Skin tone: Fitzpatrick skin type IV; lay reviewers estimated a Monk Skin Tone of 2, the lesion involves the leg, this image was taken at an angle:
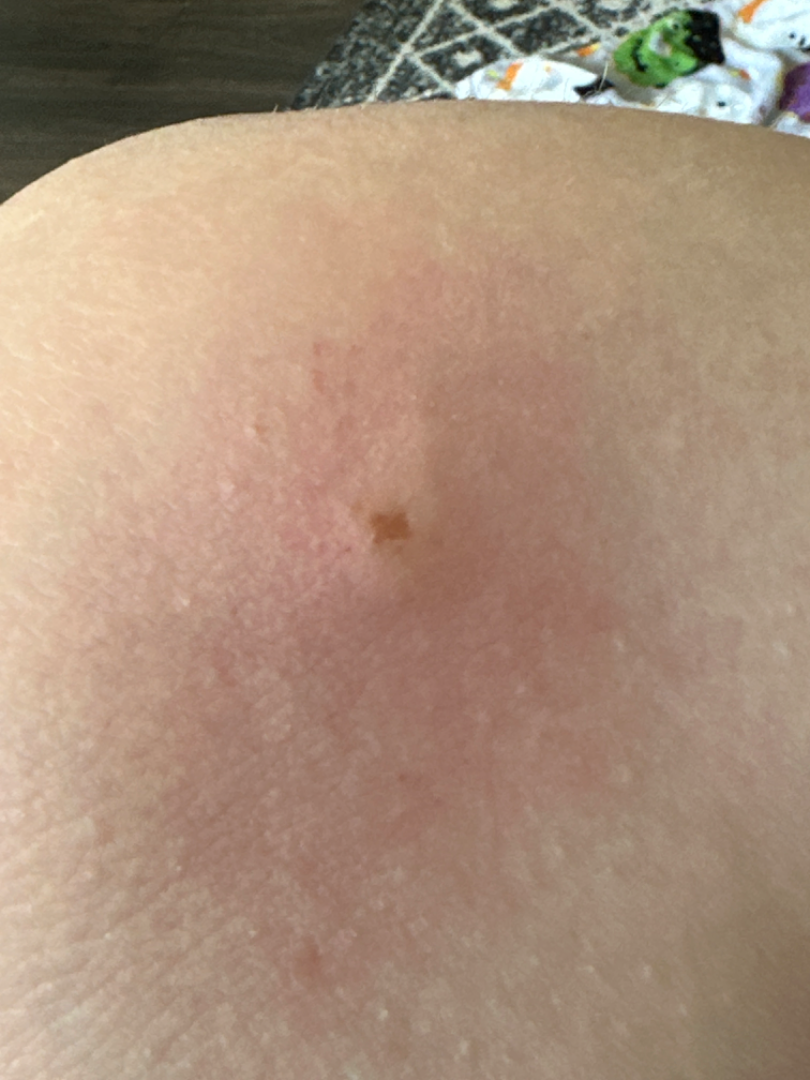<case>
  <differential>Insect Bite</differential>
</case>